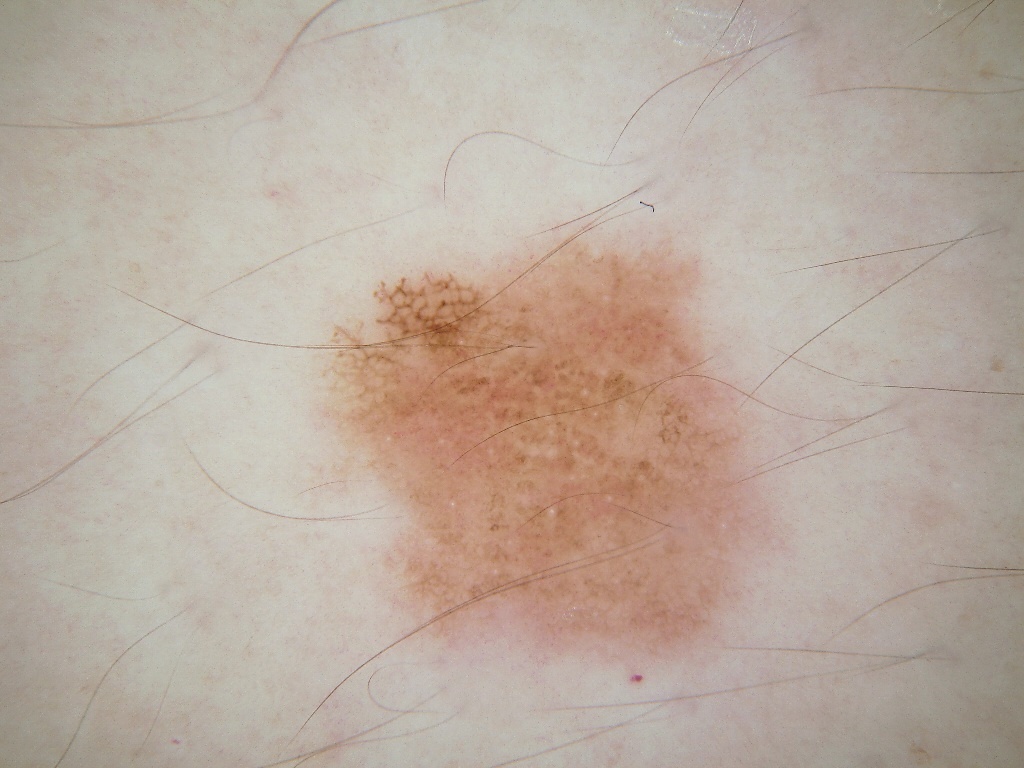Notes:
– image — dermoscopic image
– location — <box>302, 205, 795, 676</box>
– dermoscopic pattern — globules; absent: streaks
– assessment — a benign lesion